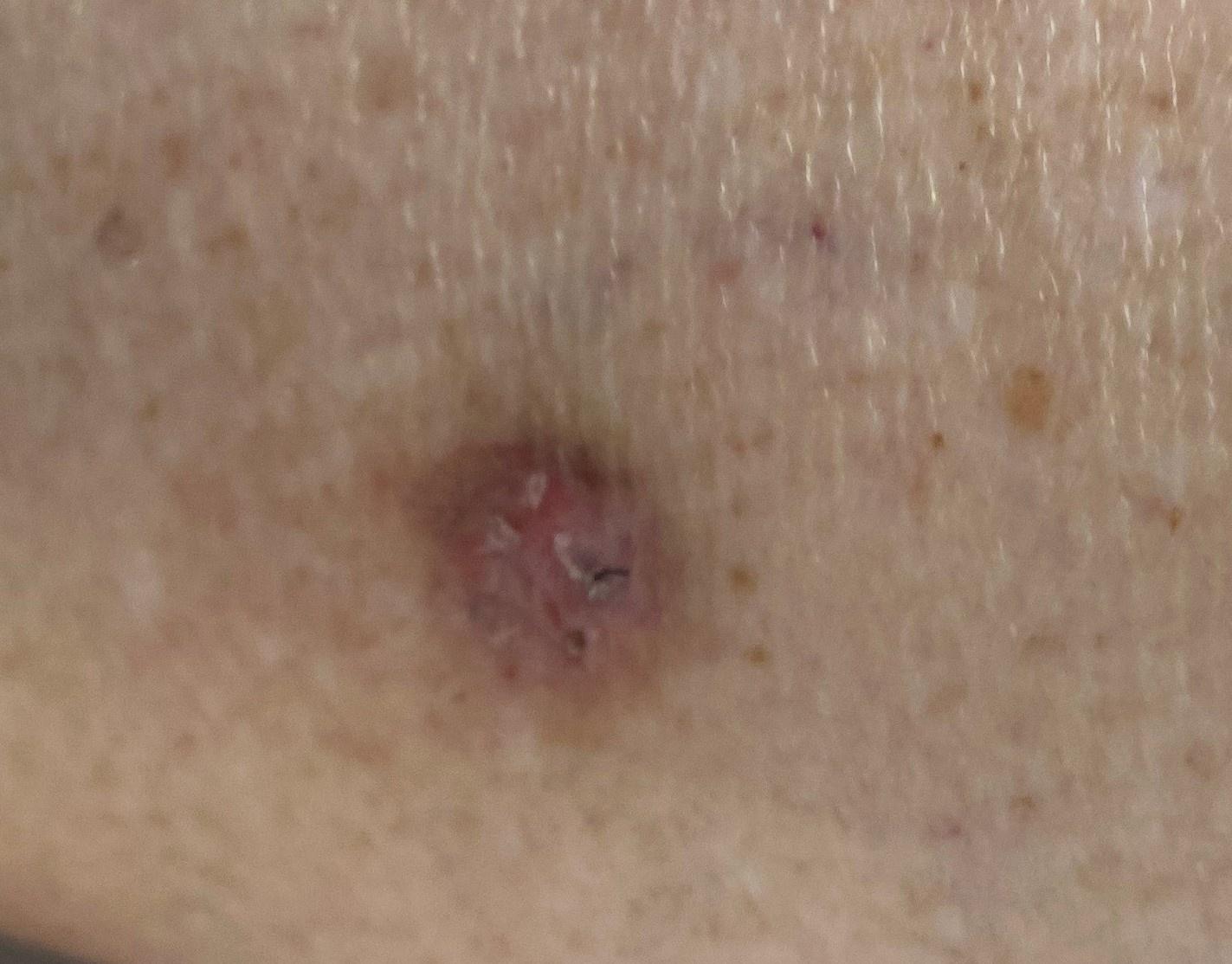Findings: A clinical photograph showing a skin lesion in context. The lesion was found on a lower extremity. Conclusion: Confirmed on histopathology as an adnexal lesion — a basal cell carcinoma.